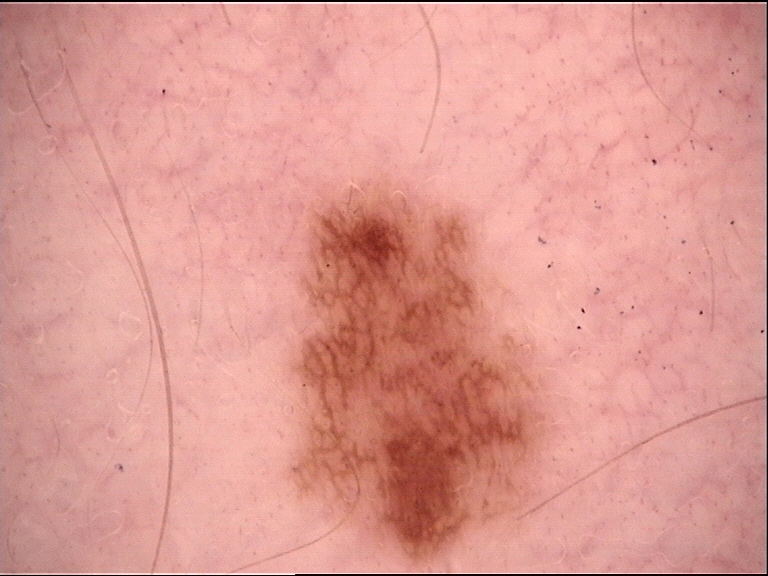Case:
• image type: dermoscopy
• class: dysplastic junctional nevus (expert consensus)